The photograph was taken at an angle, located on the arm and leg.
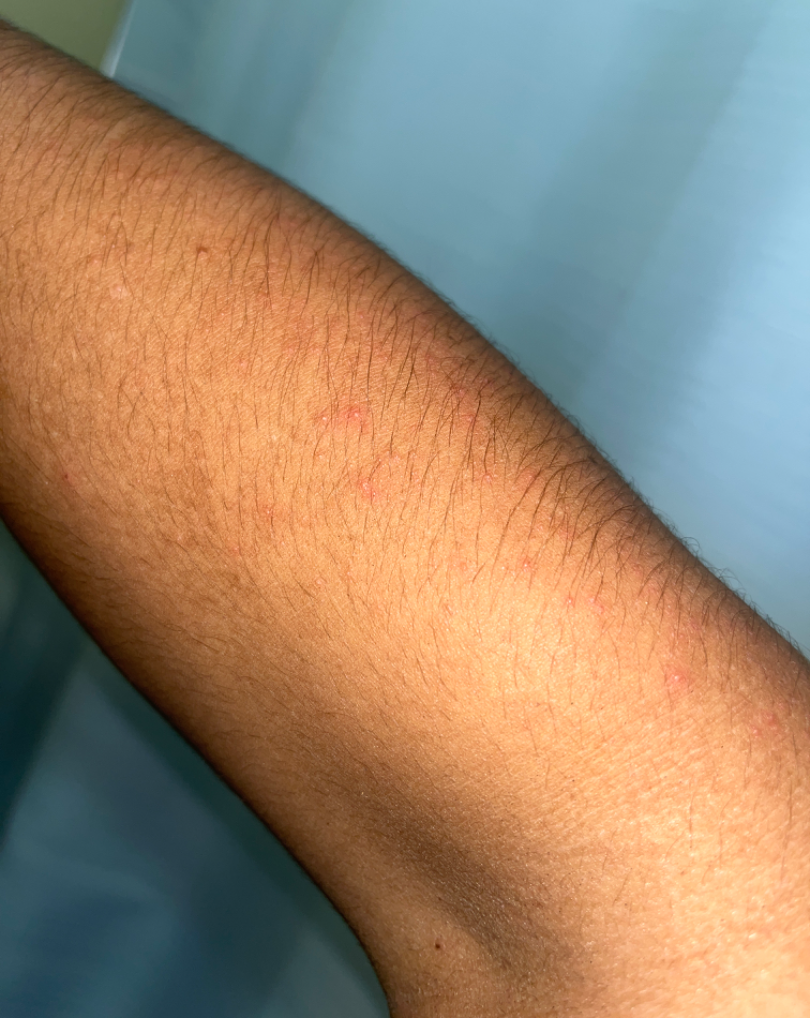The case was difficult to assess from the available photograph.